The photograph is a close-up of the affected area — 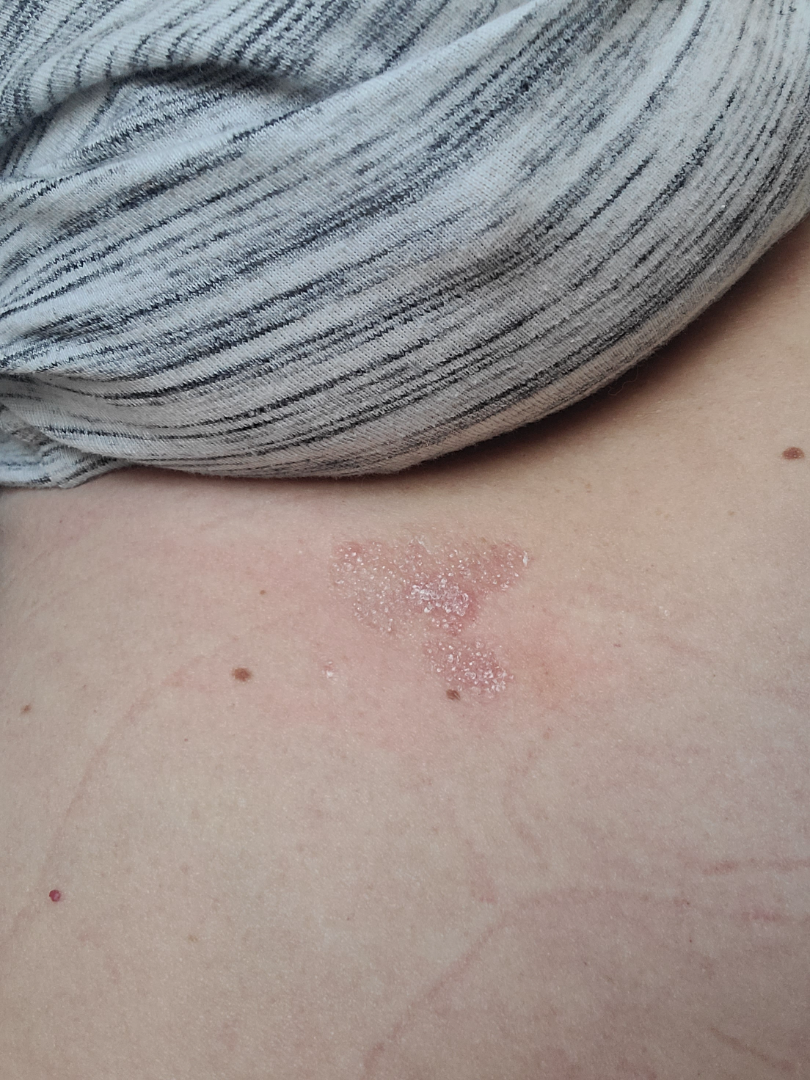{"systemic_symptoms": "none reported", "texture": "rough or flaky", "skin_tone": {"fitzpatrick": "II", "monk_skin_tone": [2, 3]}, "patient_category": "a rash", "symptoms": "itching", "duration": "one to four weeks", "differential": {"leading": ["Psoriasis"], "considered": ["Eczema"]}}